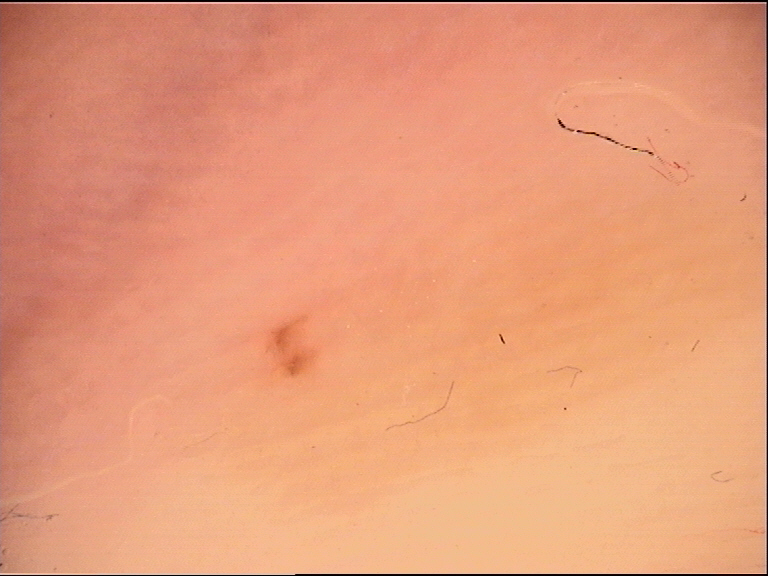A dermoscopic photograph of a skin lesion.
Consistent with a banal lesion — an acral junctional nevus.